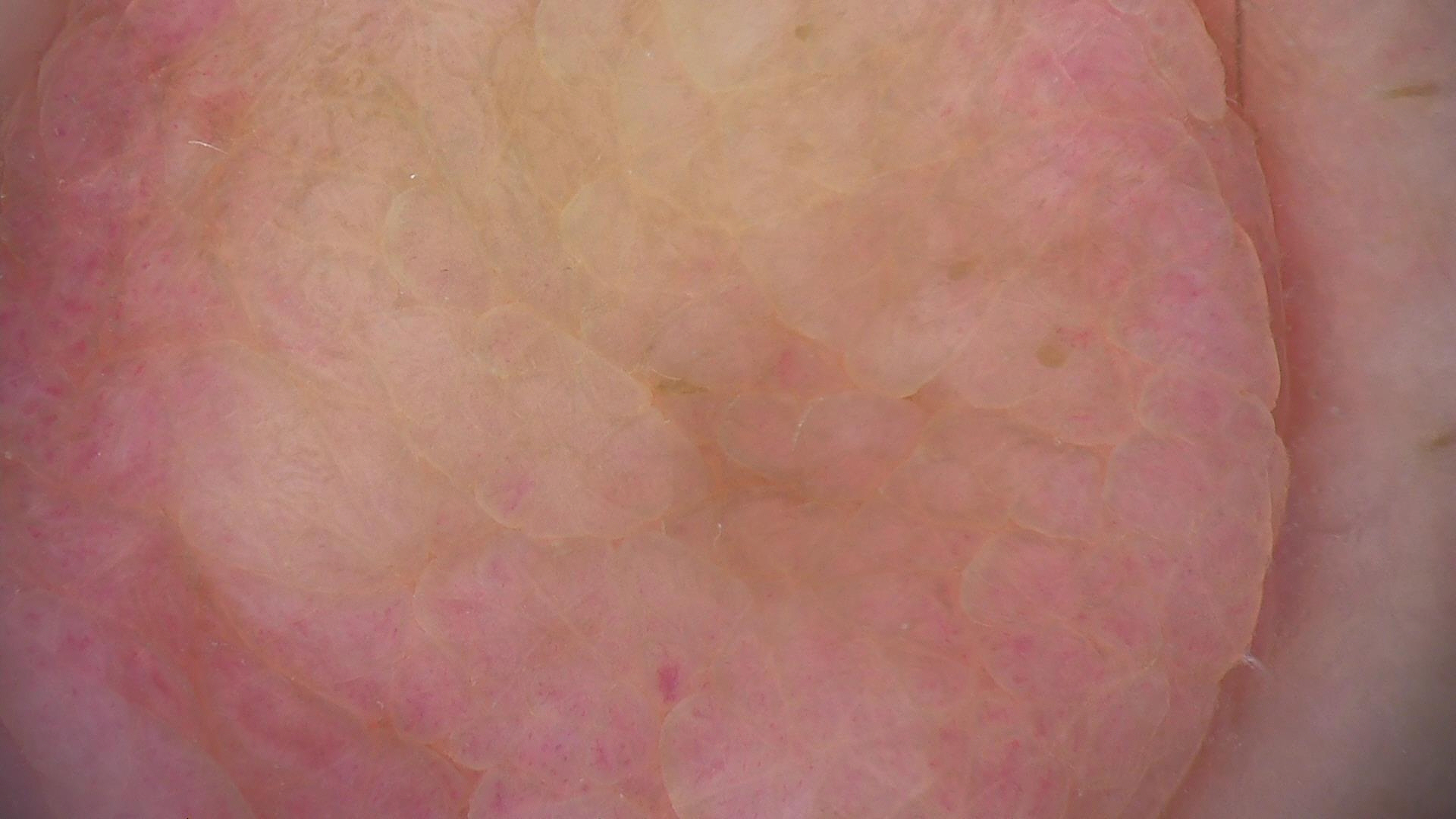Case:
Dermoscopy of a skin lesion. The morphology is that of a banal lesion.
Impression:
Labeled as a dermal nevus.